A dermoscopic photograph of a skin lesion.
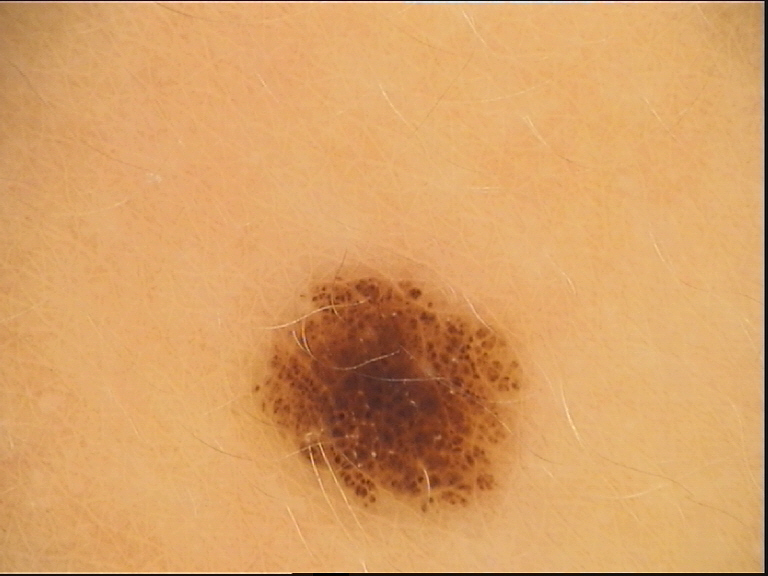diagnosis: compound nevus (expert consensus).